The subject is a female aged 40–49. Symptoms reported: burning. The arm is involved. The patient indicates the lesion is raised or bumpy. The photograph is a close-up of the affected area — 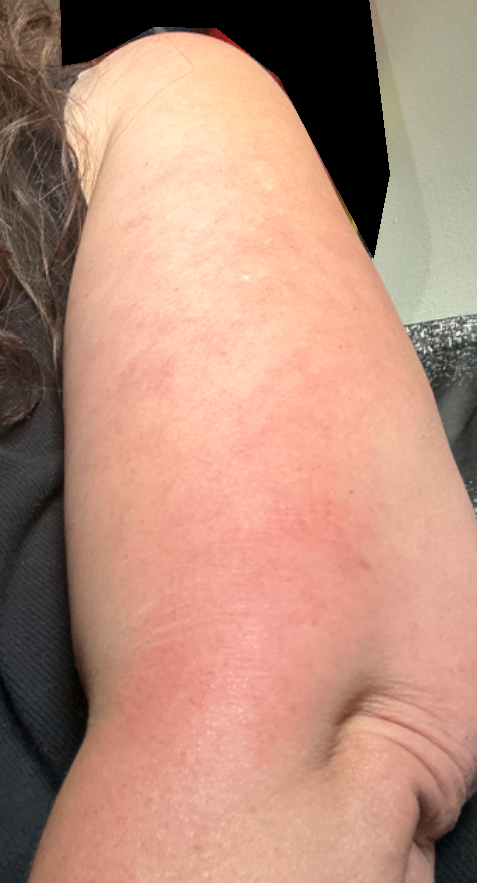| key | value |
|---|---|
| differential | the favored diagnosis is Photodermatitis; also raised was Keratosis pilaris; less likely is Allergic Contact Dermatitis |